The condition has been present for one to four weeks. The lesion is described as rough or flaky. The lesion is associated with enlargement, bothersome appearance and itching. The affected area is the front of the torso, leg and arm. A close-up photograph. The patient considered this a rash — 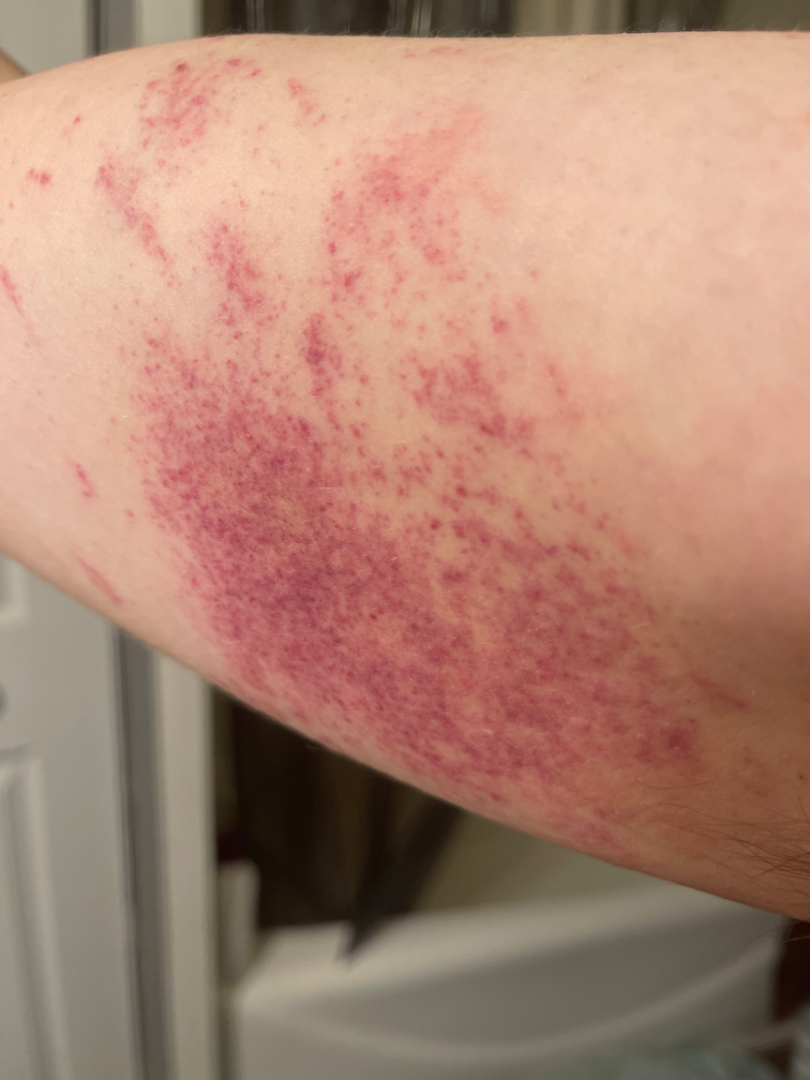On teledermatology review, the impression was split between Traumatic petechiae and ecchymoses; less likely is Abrasion, scrape, or scab.